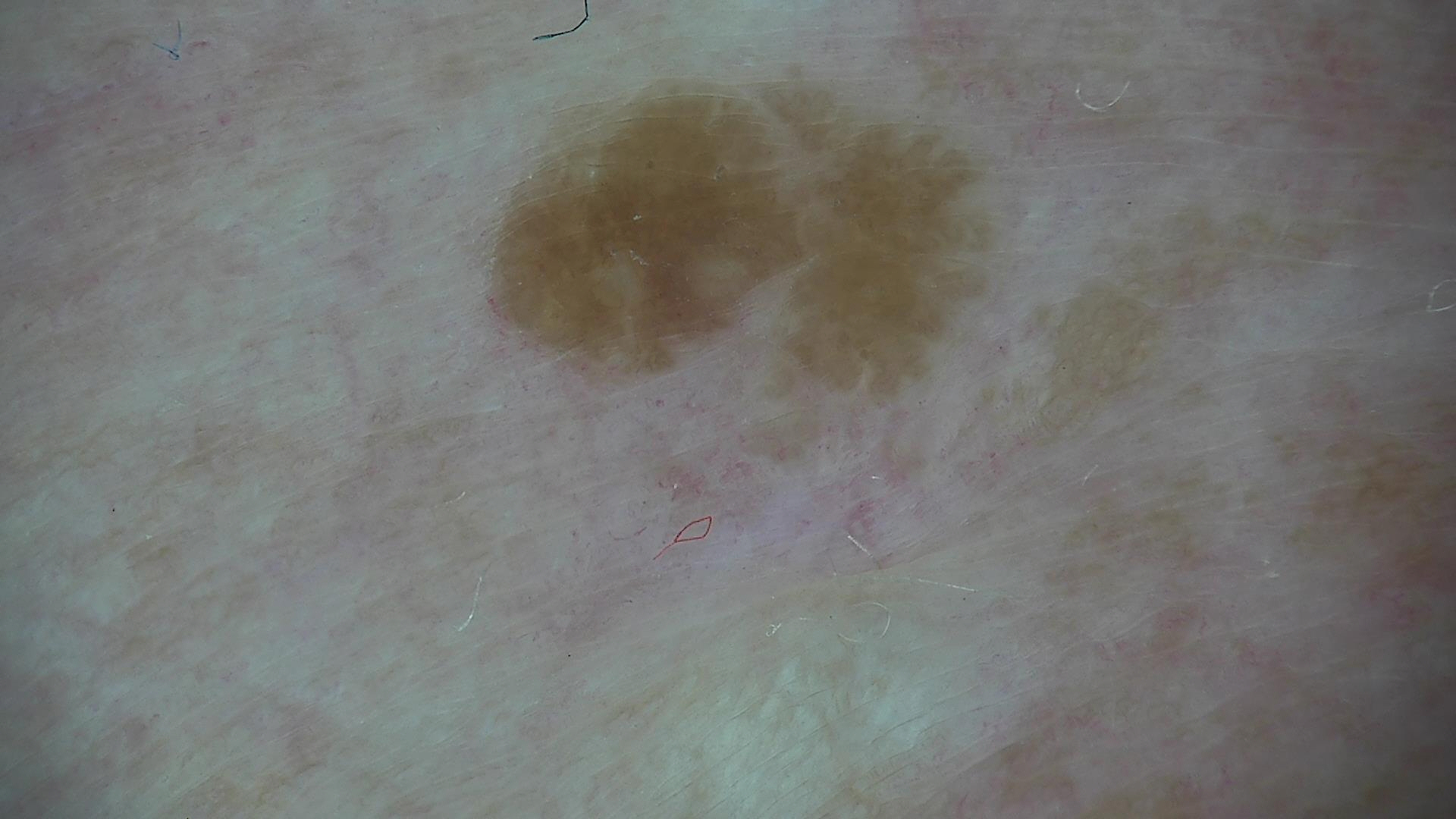label = seborrheic keratosis (expert consensus).